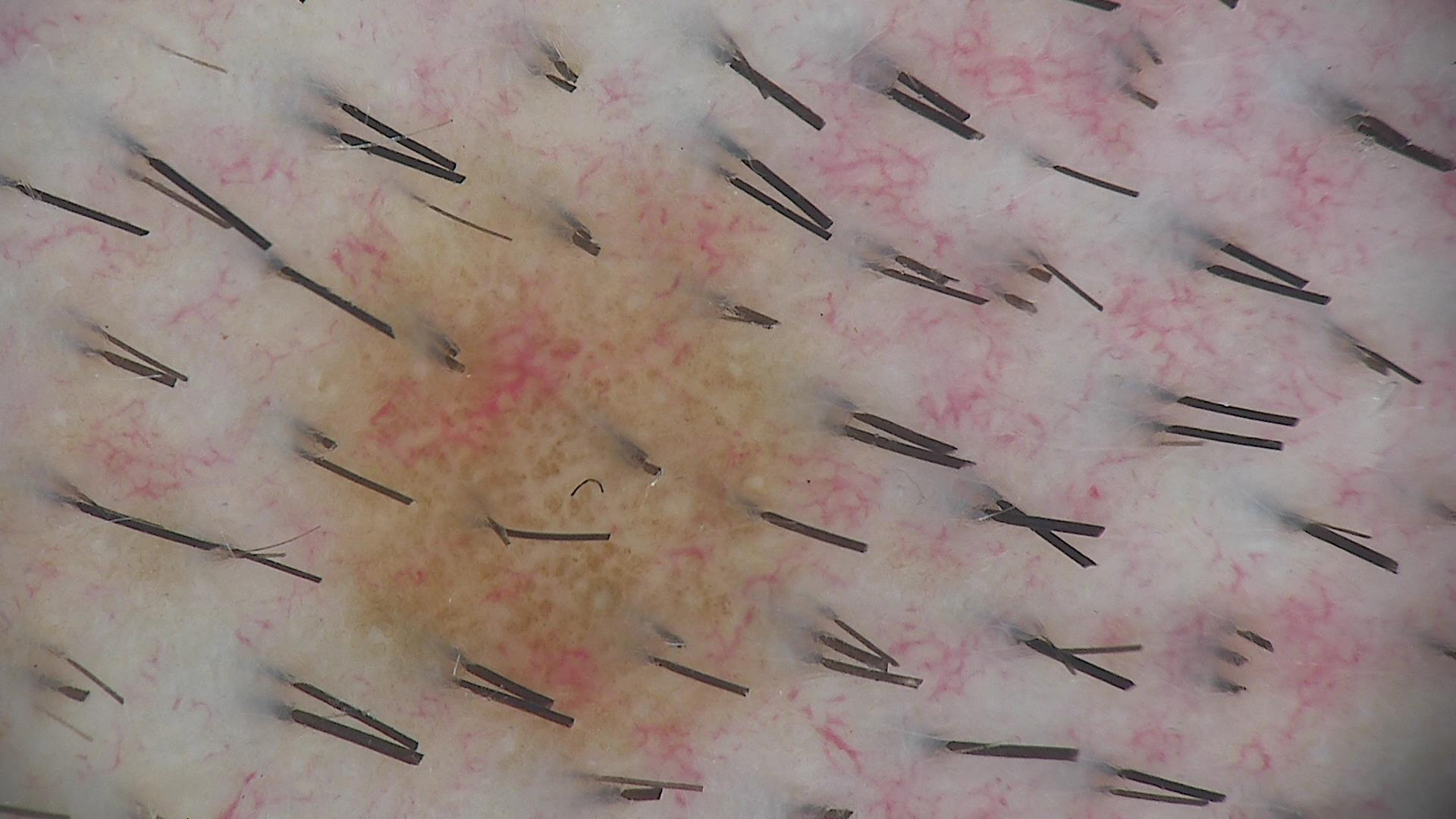Q: What kind of image is this?
A: dermatoscopy
Q: What is this lesion?
A: Miescher nevus (expert consensus)